The subject is 18–29, female; a close-up photograph; the lesion involves the arm and leg:
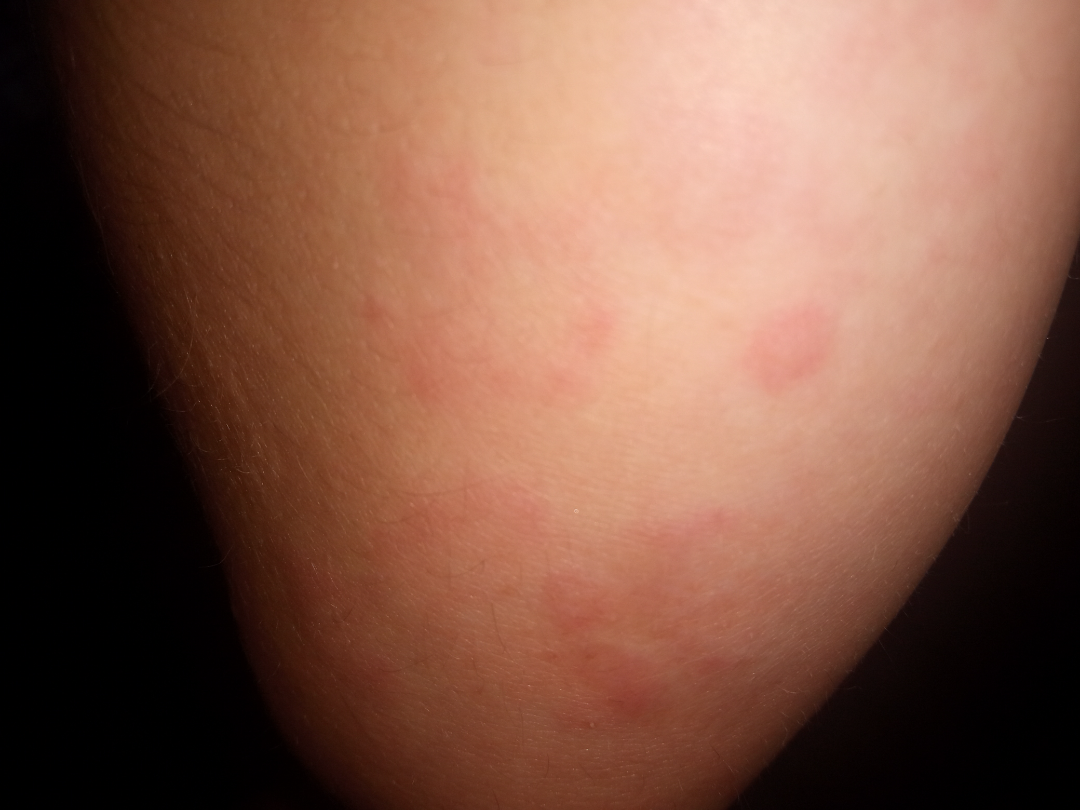Impression:
The skin findings could not be characterized from the image.
History:
Texture is reported as raised or bumpy. The lesion is associated with itching. The patient considered this a rash.